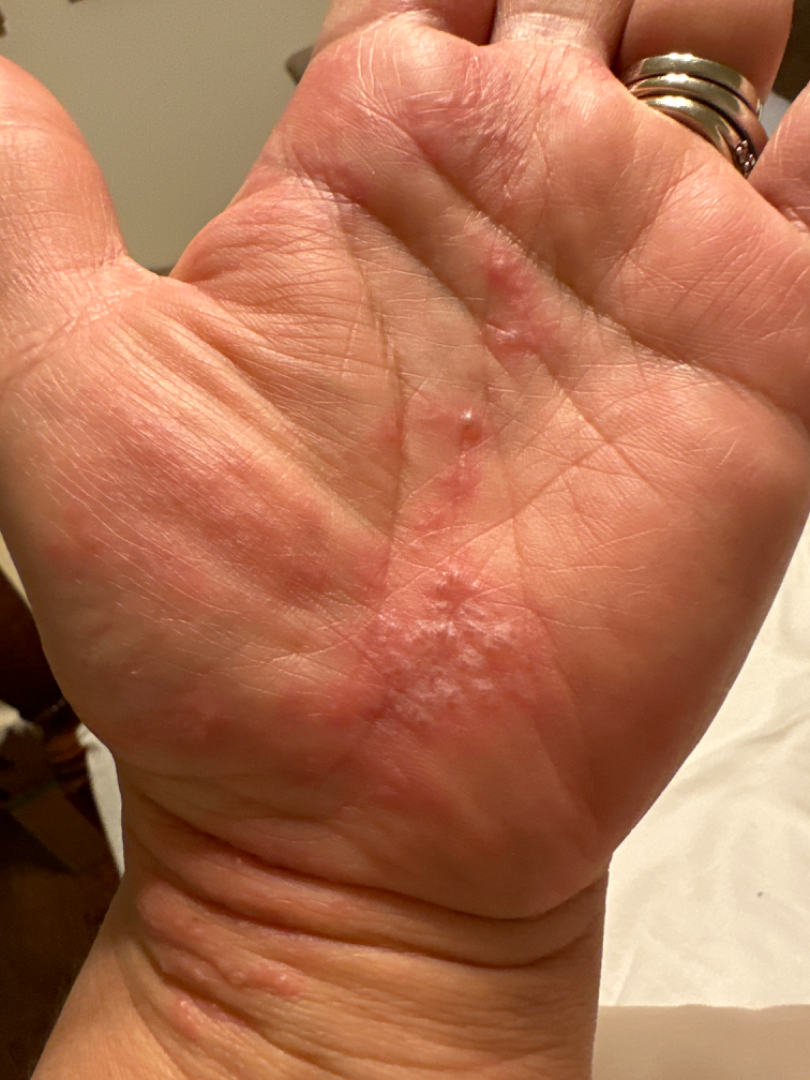History:
The photograph is a close-up of the affected area.
Impression:
Single-reviewer assessment: in keeping with Eczema.